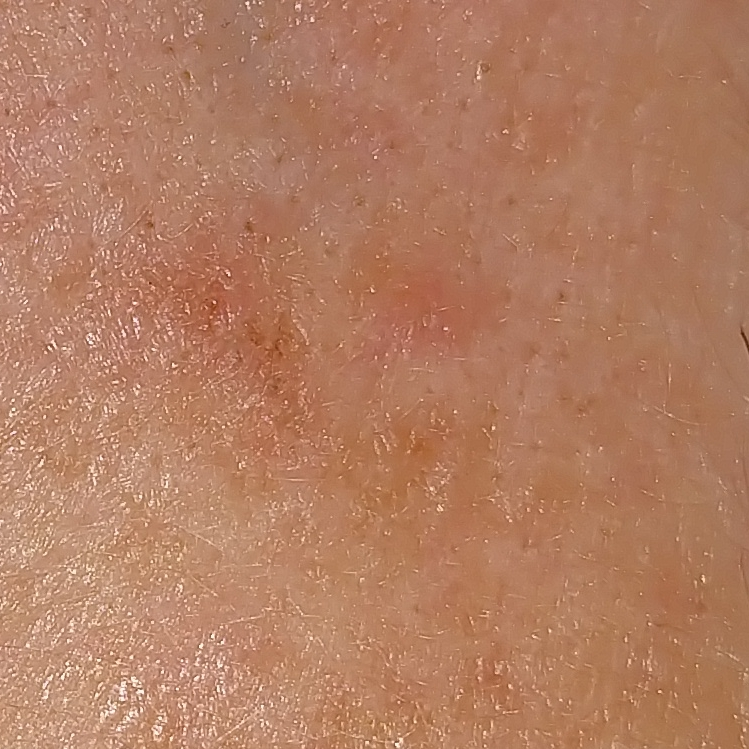Q: How was this image acquired?
A: clinical photograph
Q: Who is the patient?
A: aged 40
Q: Where on the body is the lesion?
A: the face
Q: What symptoms does the patient report?
A: growth, itching, change in appearance
Q: What is the diagnosis?
A: actinic keratosis (clinical consensus)